The photograph was taken at a distance; the affected area is the head or neck; the subject is 18–29, female: 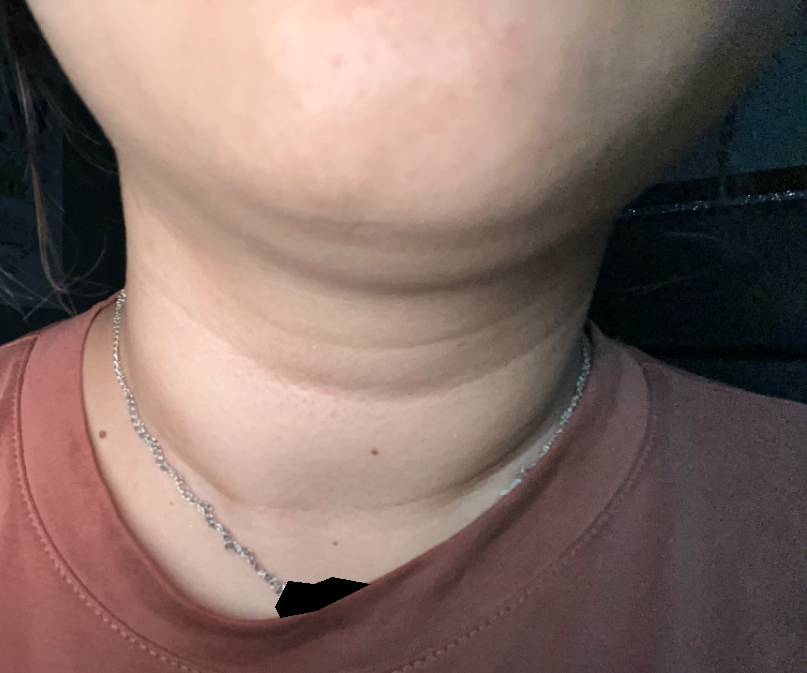{"differential": {"leading": ["Tinea Versicolor"], "unlikely": ["Seborrheic Dermatitis", "Eczema", "Tinea"]}}